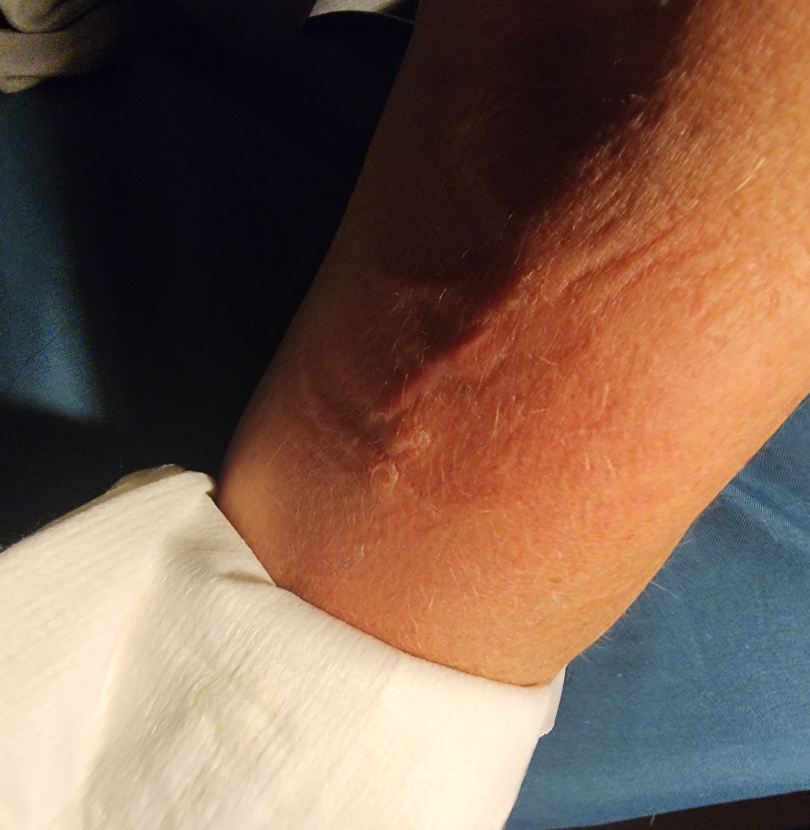The skin condition could not be confidently assessed from this image. No associated systemic symptoms reported. The patient is a female aged 40–49. The photo was captured at an angle. The lesion is described as fluid-filled. The affected area is the arm. The patient described the issue as a rash. The patient notes pain, burning and itching. The condition has been present for about one day.